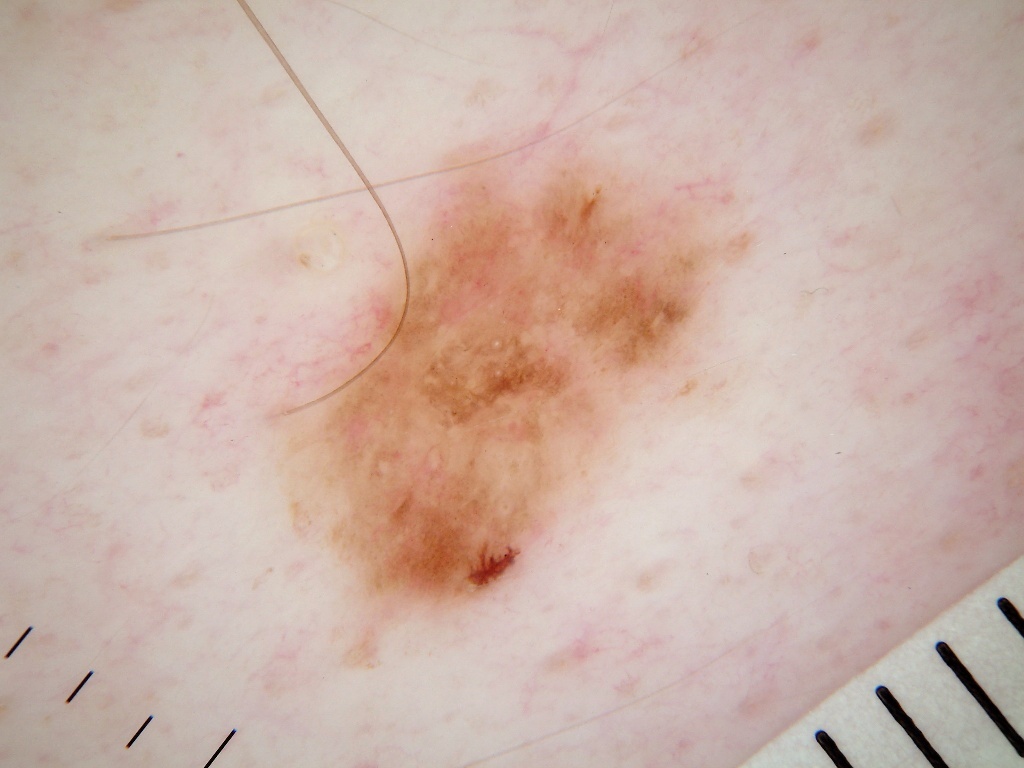Findings:
A male patient, in their 50s. A dermoscopic close-up of a skin lesion. Dermoscopic examination shows pigment network and milia-like cysts, with no streaks, negative network, or globules. As (left, top, right, bottom), the lesion is bounded by [249,113,776,684].
Impression:
Clinically diagnosed as a melanocytic nevus.